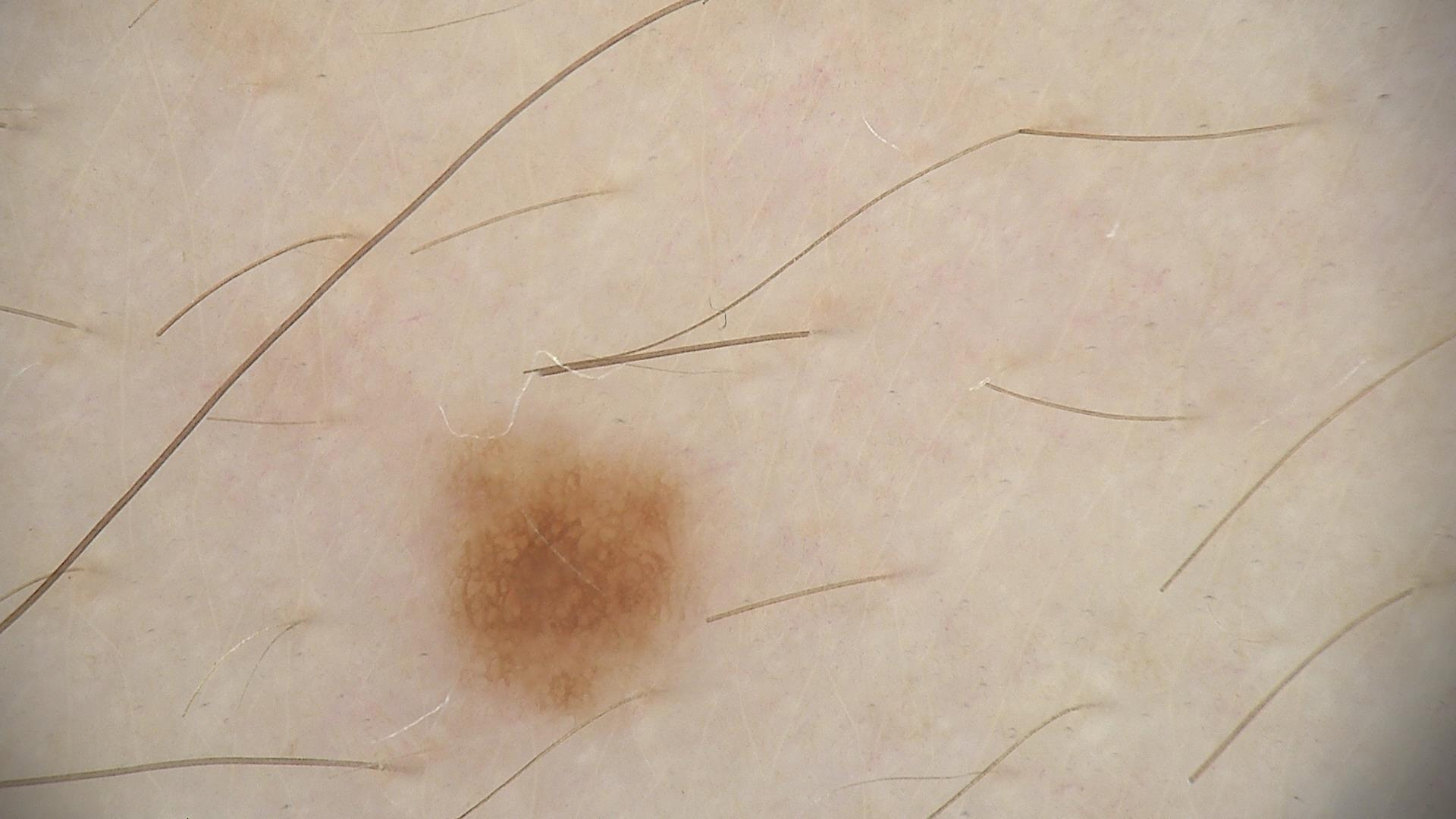A dermatoscopic image of a skin lesion.
Labeled as a benign lesion — a dysplastic junctional nevus.